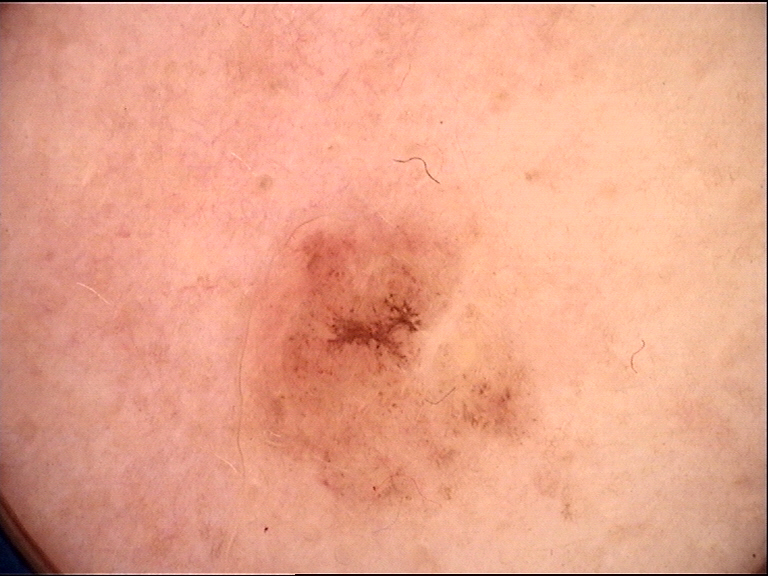Findings:
– imaging — dermoscopy
– diagnosis — dysplastic junctional nevus (expert consensus)